Fitzpatrick II · a clinical photograph showing a skin lesion in context · a male patient aged 73 to 77:
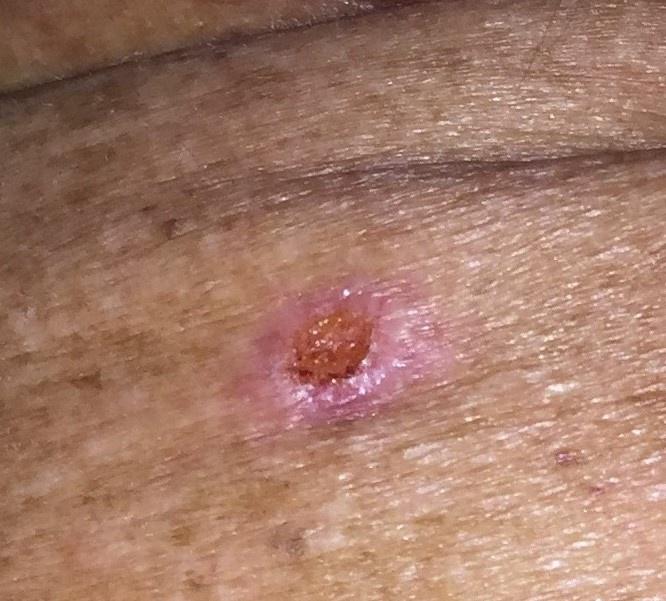Case summary:
The lesion was found on the trunk.
Conclusion:
On biopsy, the diagnosis was a basal cell carcinoma.